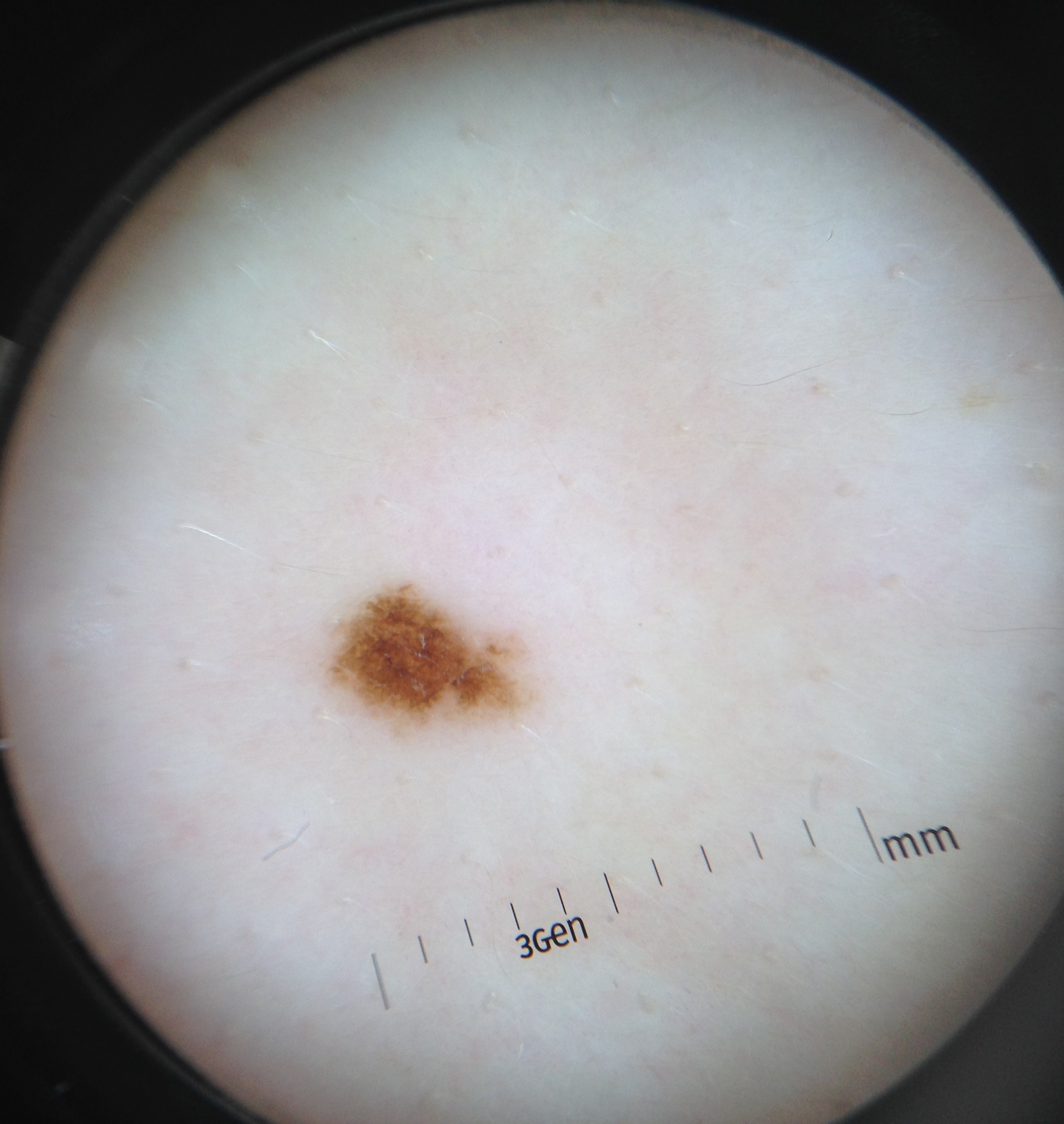The diagnostic label was a dysplastic junctional nevus.